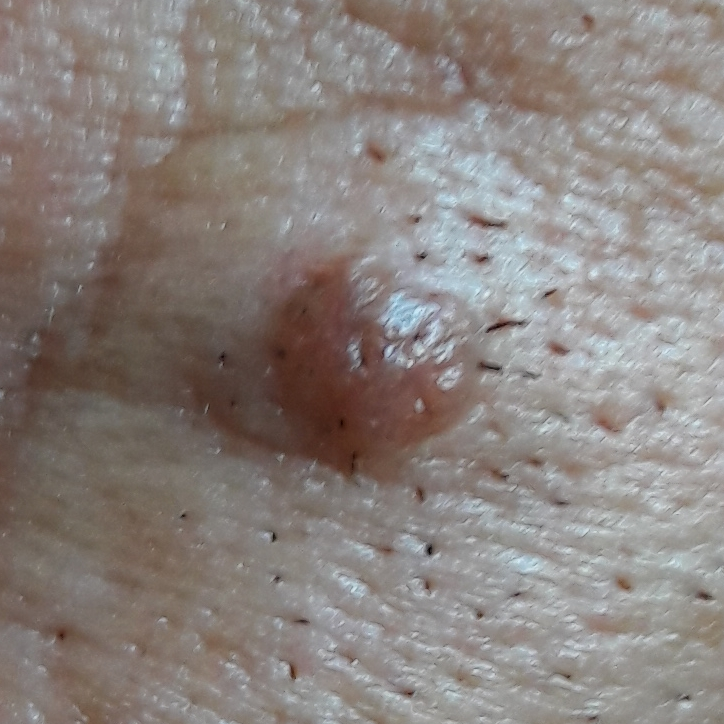Case summary:
A clinical photograph showing a skin lesion. A subject 44 years of age. The lesion is on the face.
Conclusion:
Clinically diagnosed as a nevus.